A dermoscopic image of a skin lesion:
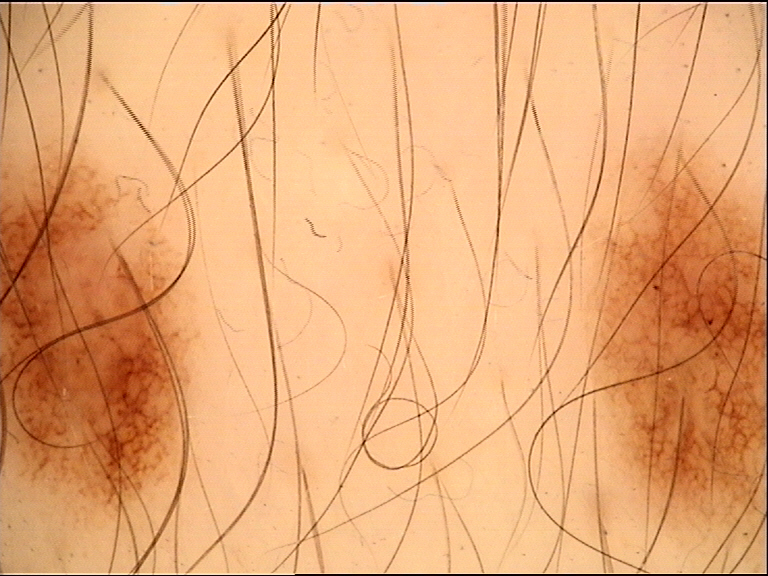Consistent with a dysplastic junctional nevus.